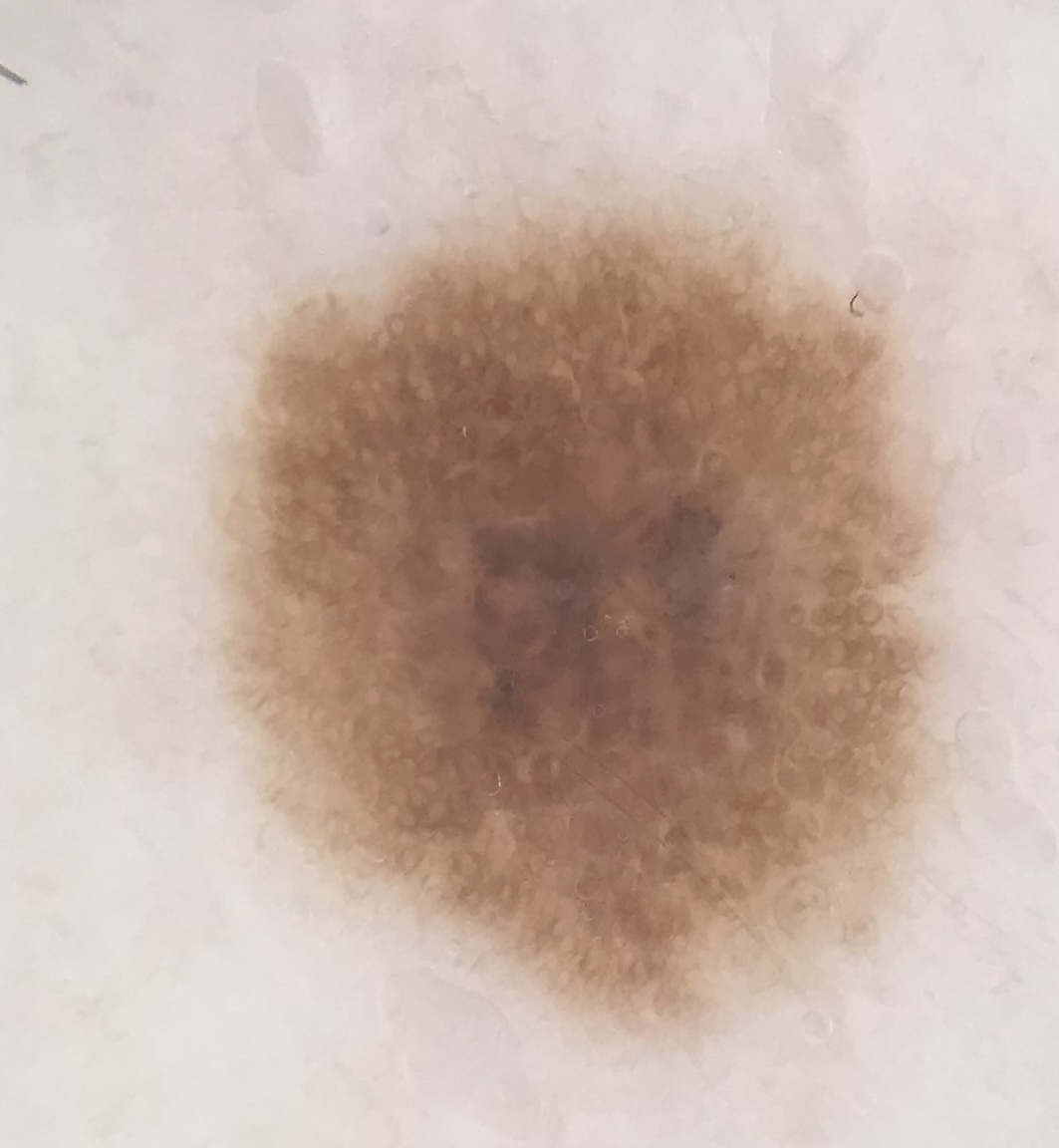diagnostic label: dysplastic junctional nevus (expert consensus).